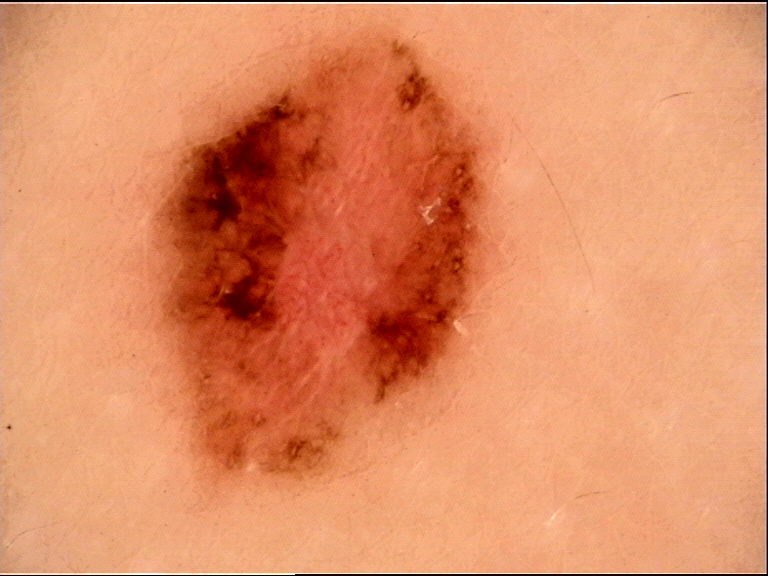| feature | finding |
|---|---|
| image | dermatoscopy |
| diagnostic label | melanoma (biopsy-proven) |